The patient says their skin reddens with sun exposure; acquired for a research image collection, with no referral diagnosis; a moderate number of moles by the patient's own estimate; by self-report, a personal history of cancer, a personal history of skin cancer, and no family history of skin cancer; a male subject age 77; dermoscopy of a skin lesion.
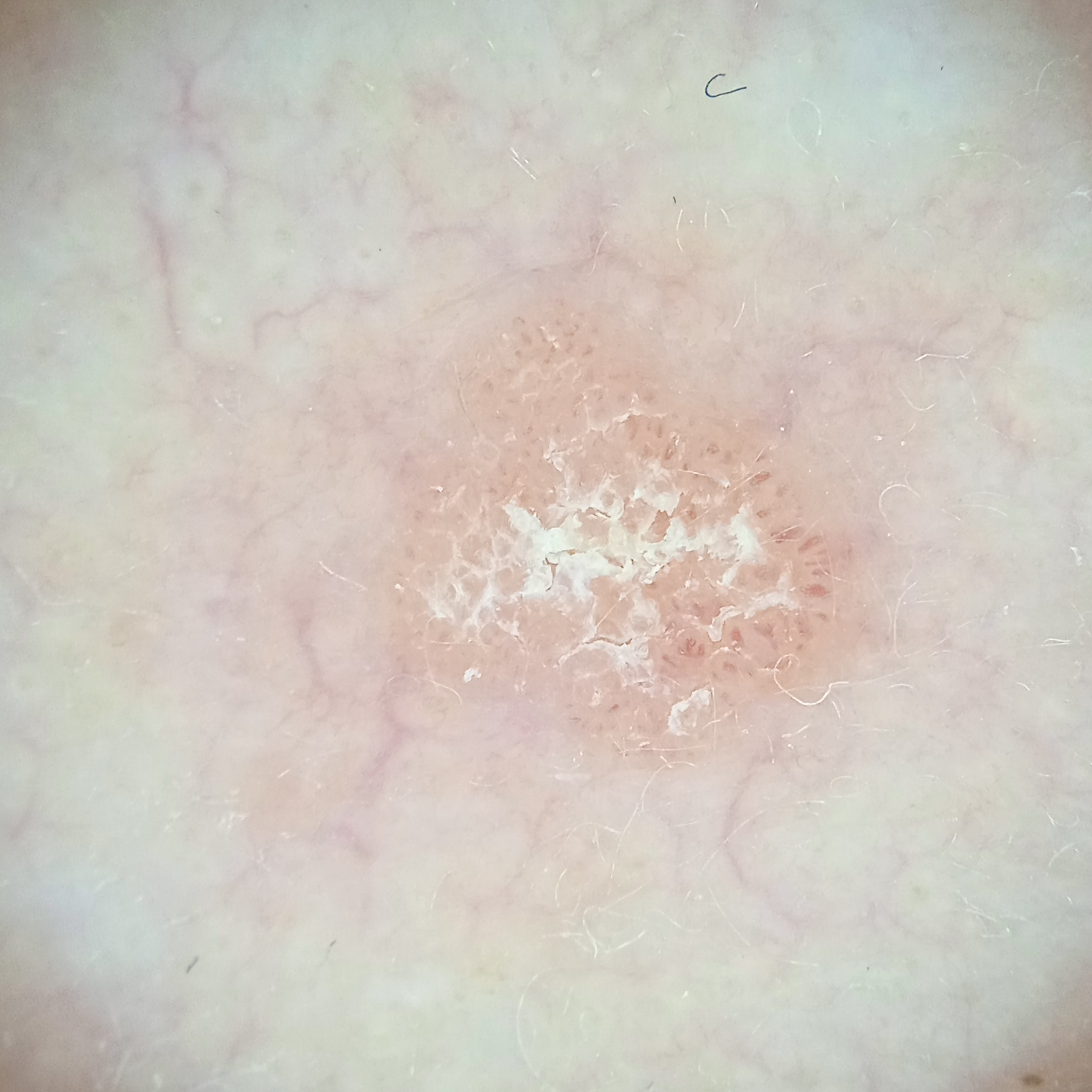site=the face; lesion size=4.3 mm; diagnostic label=actinic keratosis (dermatologist consensus).